The condition has been present for less than one week, the back of the hand is involved, the lesion is described as raised or bumpy, self-categorized by the patient as a rash, the patient reports burning and itching, the photograph is a close-up of the affected area, the patient reported no systemic symptoms:
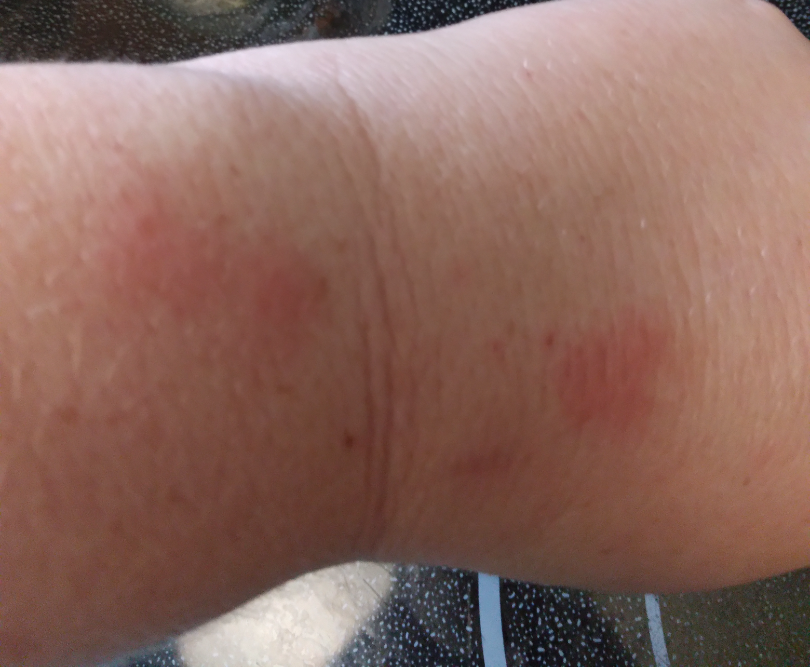assessment: indeterminate from the photograph.